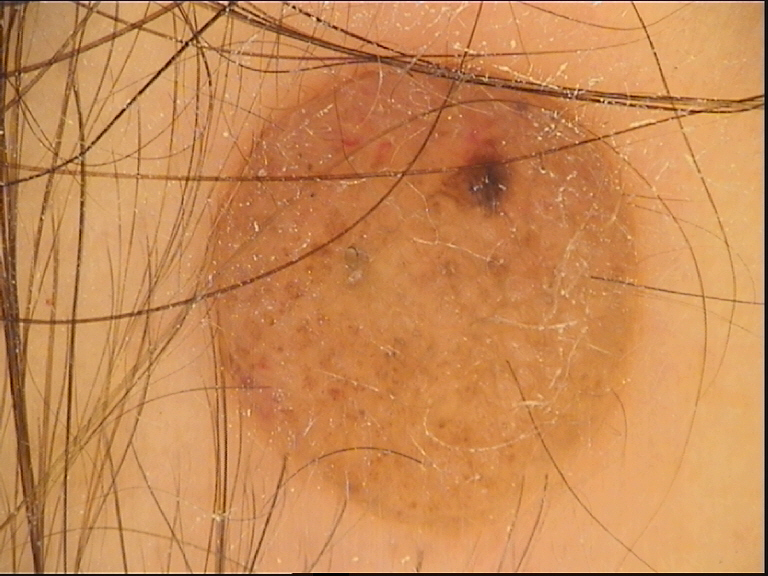The morphology is that of a banal lesion. Classified as a dermal nevus.